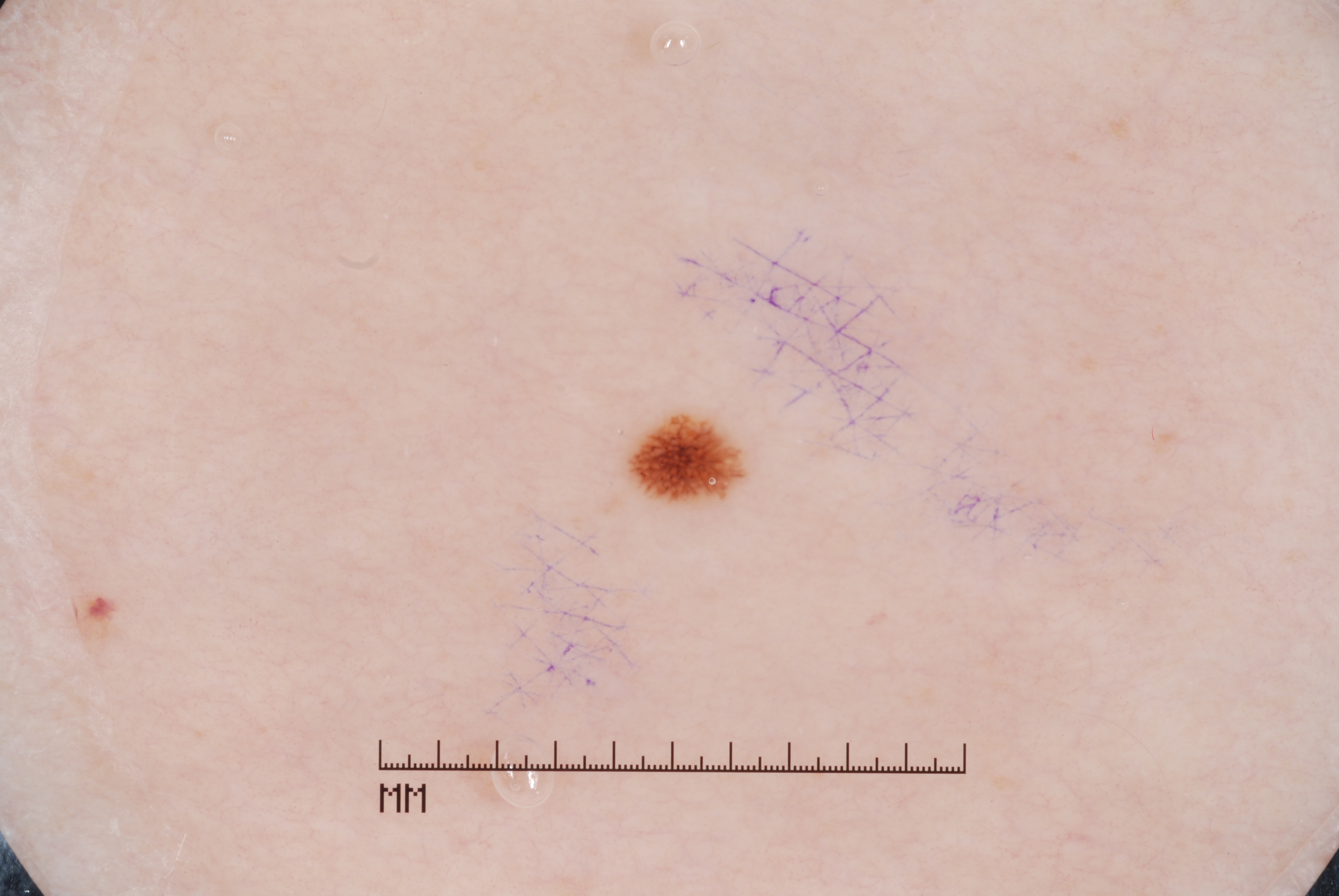• patient · female, aged around 45
• image · dermoscopy of a skin lesion
• dermoscopic pattern · pigment network
• lesion bbox · [638, 421, 732, 497]
• assessment · a melanocytic nevus, a benign skin lesion